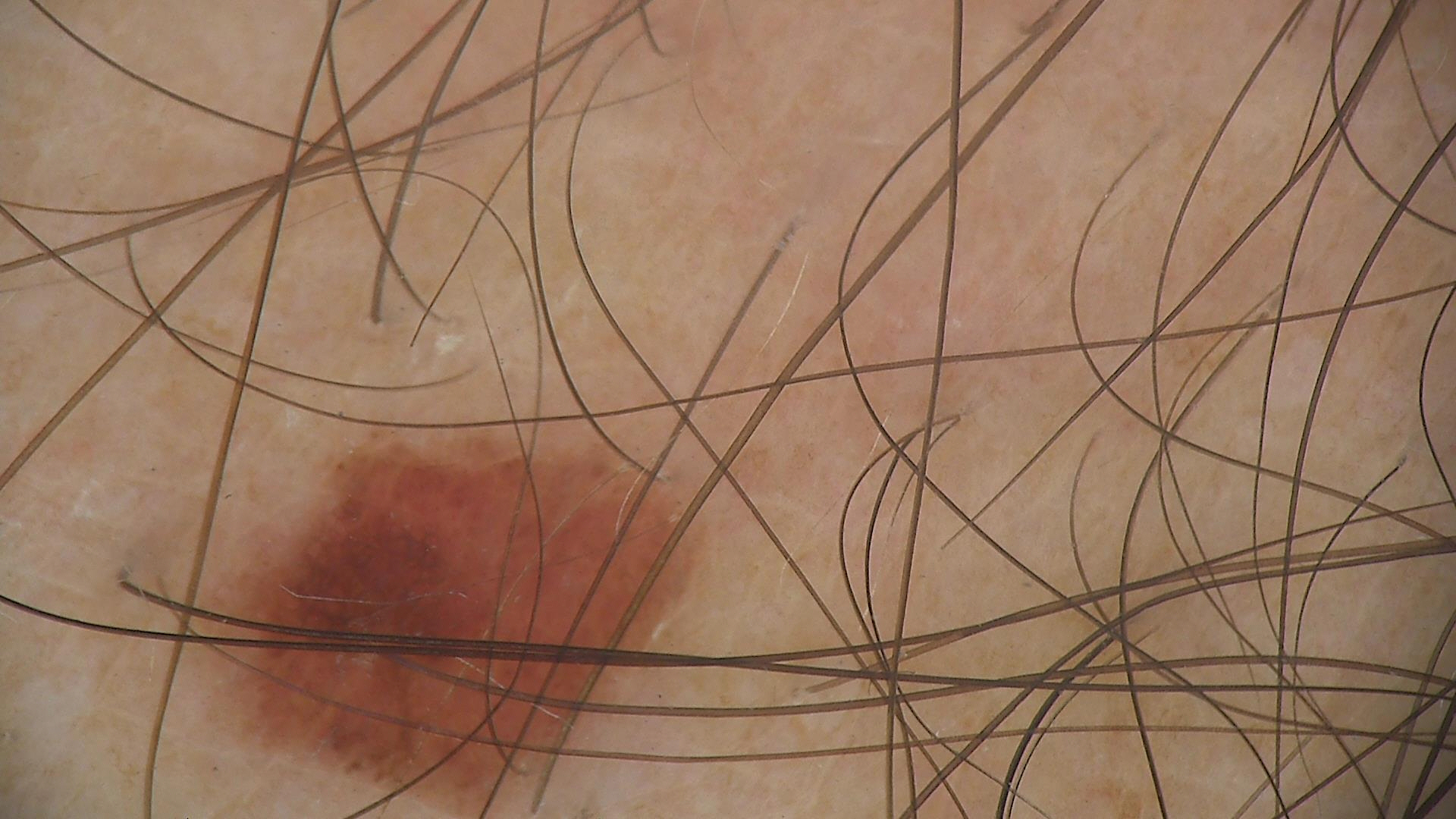class = dysplastic junctional nevus (expert consensus).